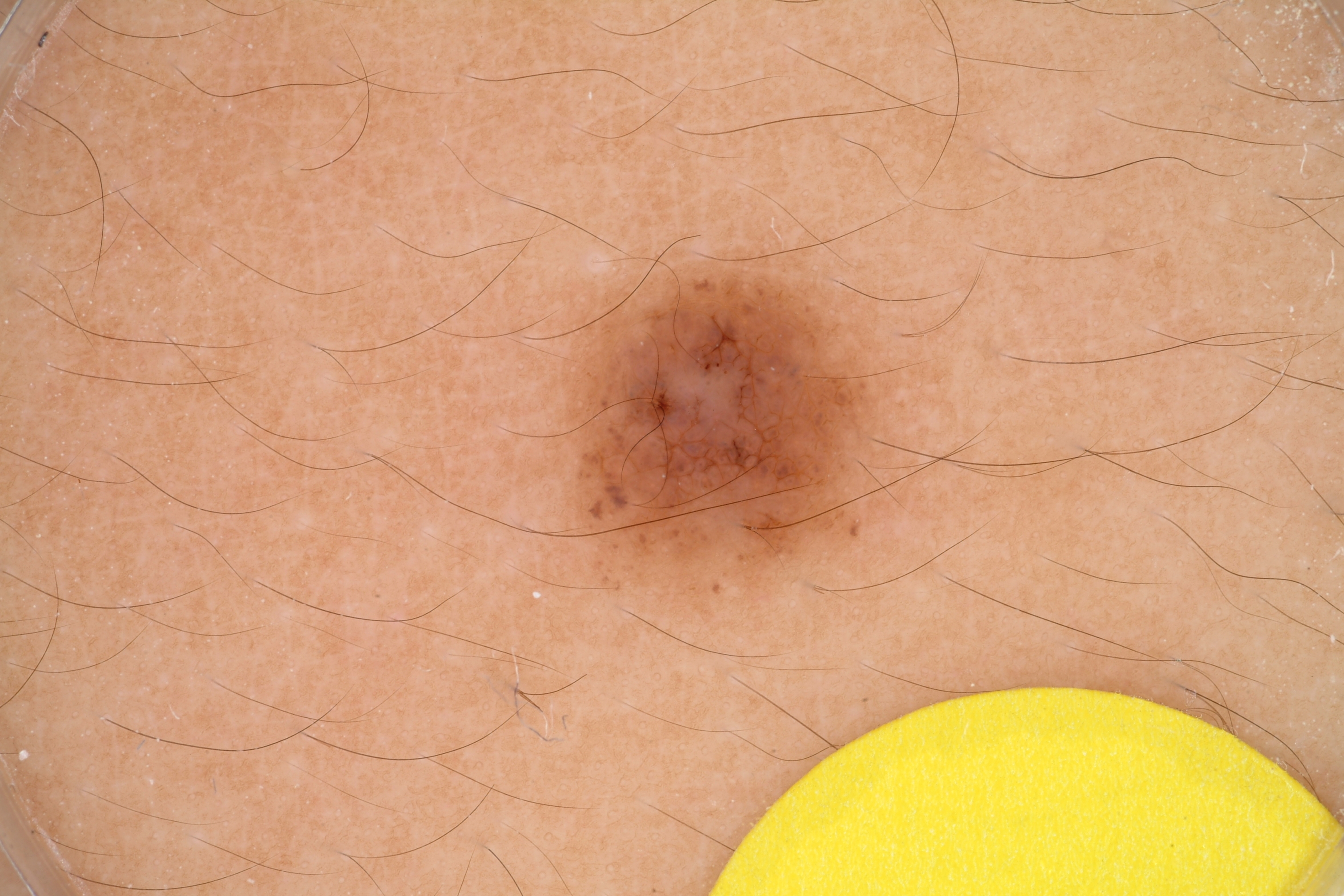patient:
  sex: male
  age_approx: 15
image:
  modality: dermoscopy
dermoscopic_features:
  present:
    - pigment network
  absent:
    - streaks
    - globules
    - negative network
    - milia-like cysts
lesion_location:
  bbox_xyxy:
    - 547
    - 253
    - 895
    - 599
lesion_extent:
  approx_field_fraction_pct: 7
diagnosis:
  name: melanocytic nevus
  malignancy: benign
  lineage: melanocytic
  provenance: clinical